Collected as part of a research study, without a referral diagnosis. The patient describes having numerous moles. The patient says their skin reddens with sun exposure. A female subject 54 years of age. A dermoscopic image of a skin lesion.
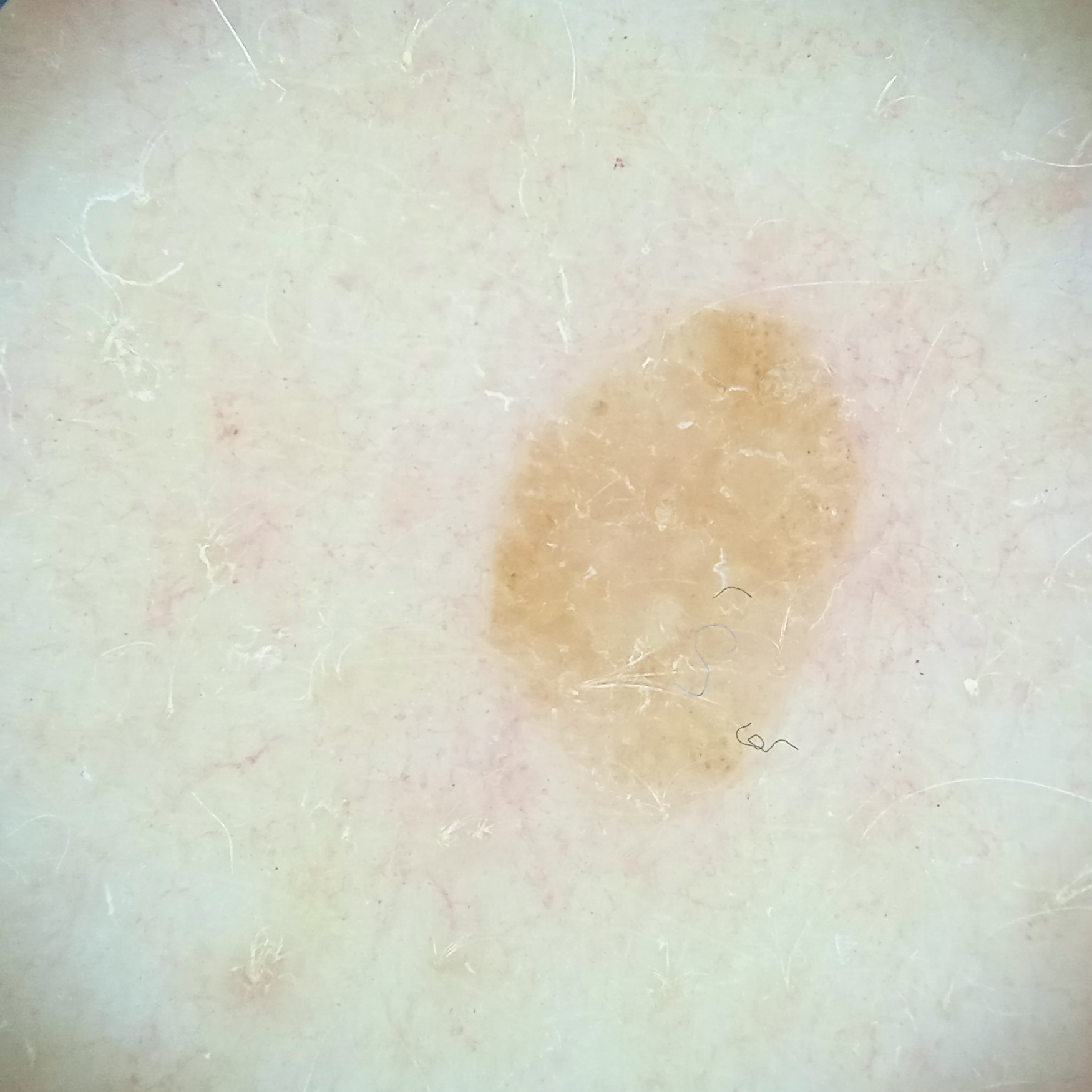{
  "lesion_location": "the back",
  "lesion_size": {
    "diameter_mm": 5.5
  },
  "diagnosis": {
    "name": "seborrheic keratosis",
    "malignancy": "benign"
  }
}